An image taken at an angle.
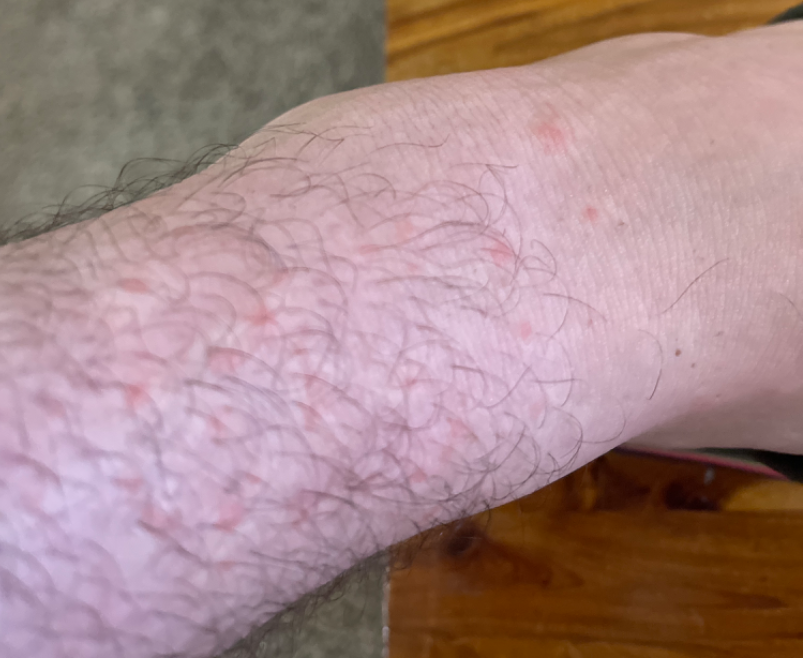skin tone: Fitzpatrick phototype II; lay reviewers estimated Monk skin tone scale 2 | differential diagnosis: Lichen planus/lichenoid eruption (considered); Insect Bite (considered); Allergic Contact Dermatitis (considered).